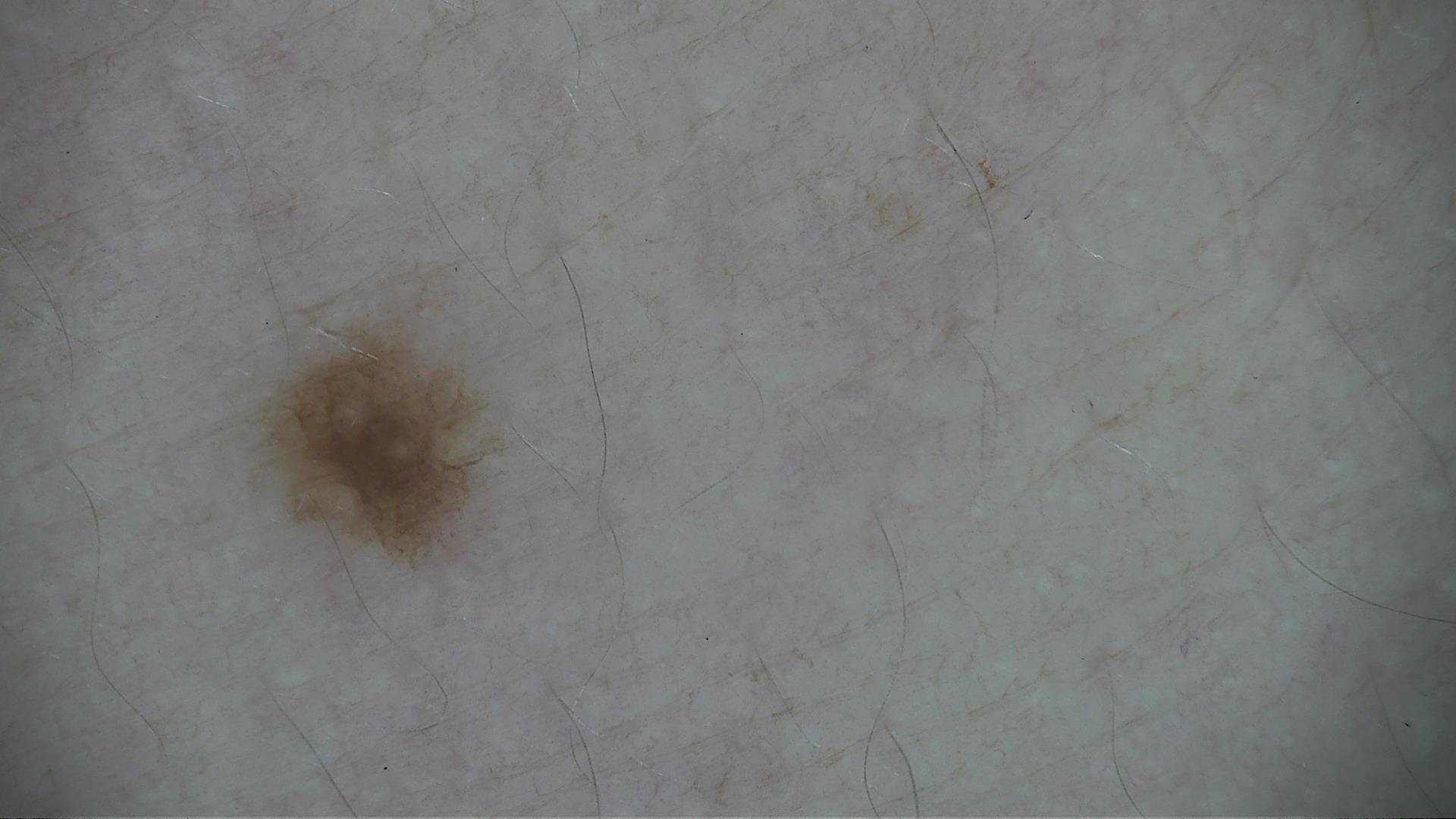diagnosis:
  name: dysplastic junctional nevus
  code: jd
  malignancy: benign
  super_class: melanocytic
  confirmation: expert consensus